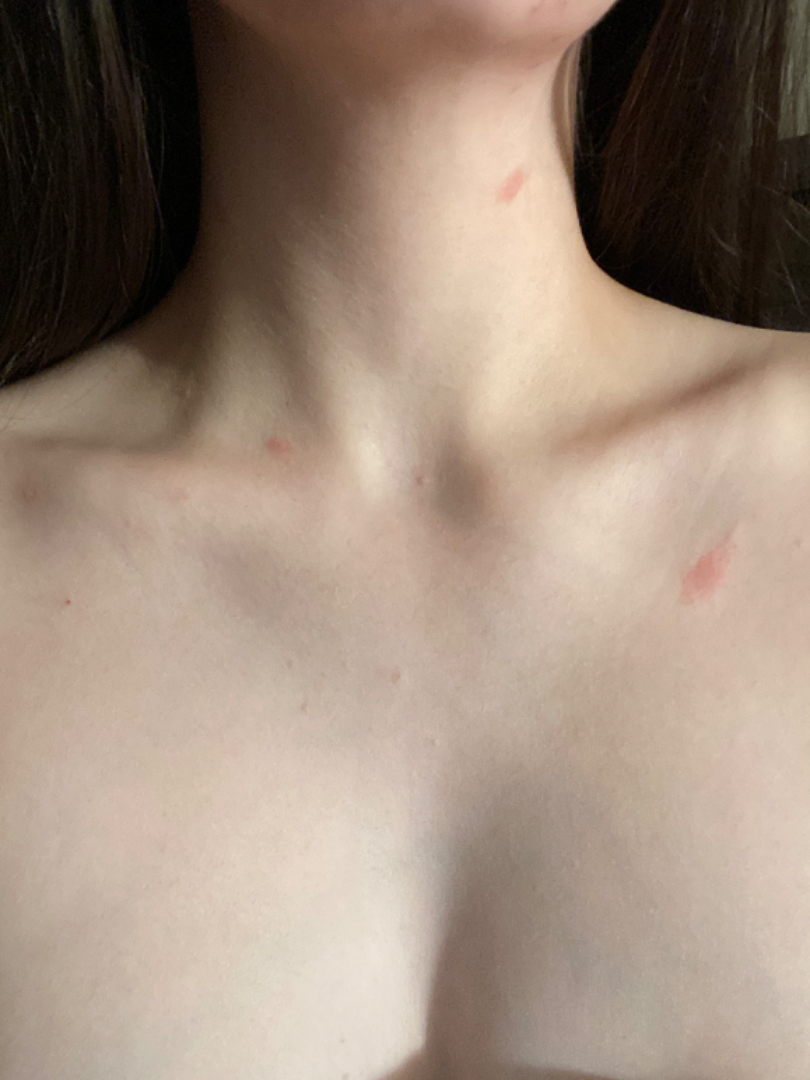assessment: could not be assessed | surface texture: rough or flaky and raised or bumpy | self-categorized as: a rash | framing: close-up | subject: female, age 18–29 | symptom duration: less than one week | systemic symptoms: none reported | body site: front of the torso and head or neck.